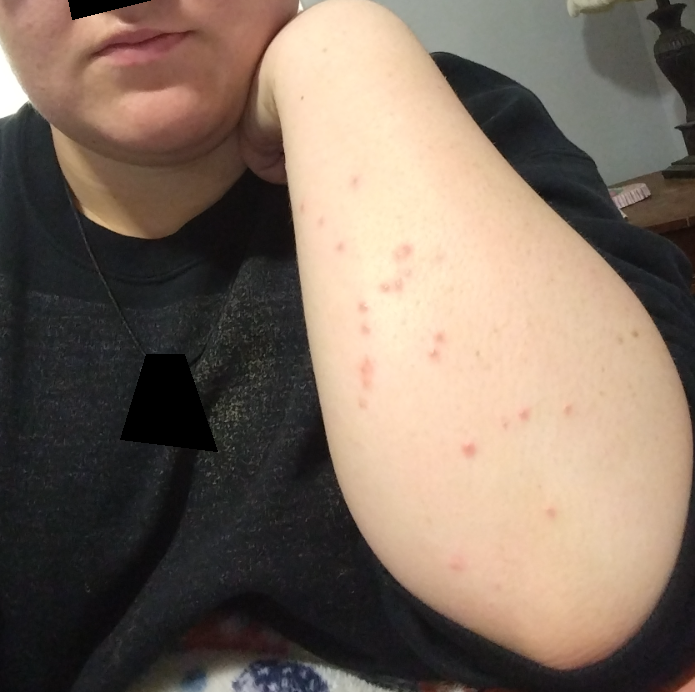On photographic review, the leading consideration is Insect Bite.